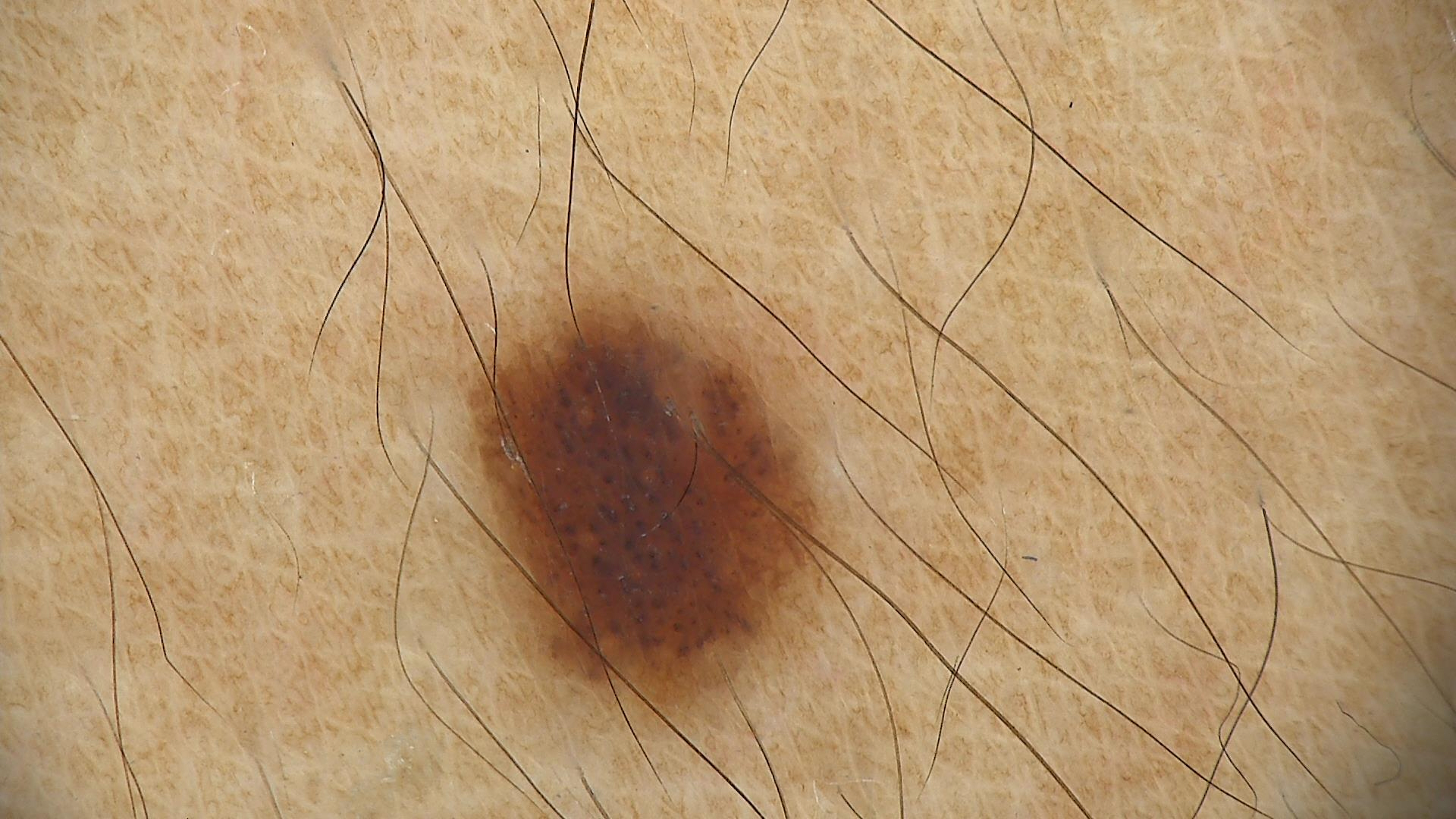Diagnosed as a compound nevus.